Self-categorized by the patient as a rash; the patient reported no relevant symptoms from the lesion; the lesion involves the arm, back of the hand and head or neck; this image was taken at an angle; the condition has been present for one to four weeks; the lesion is described as raised or bumpy:
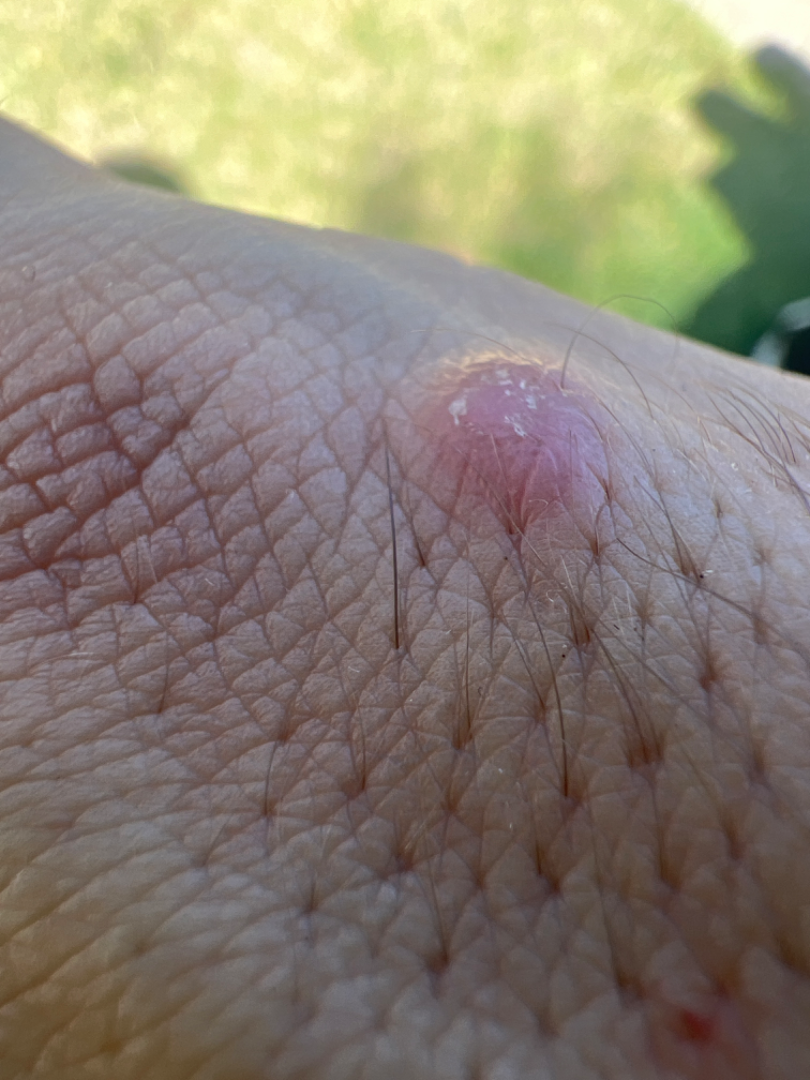Most likely Actinic Keratosis; the differential also includes Prurigo nodularis.